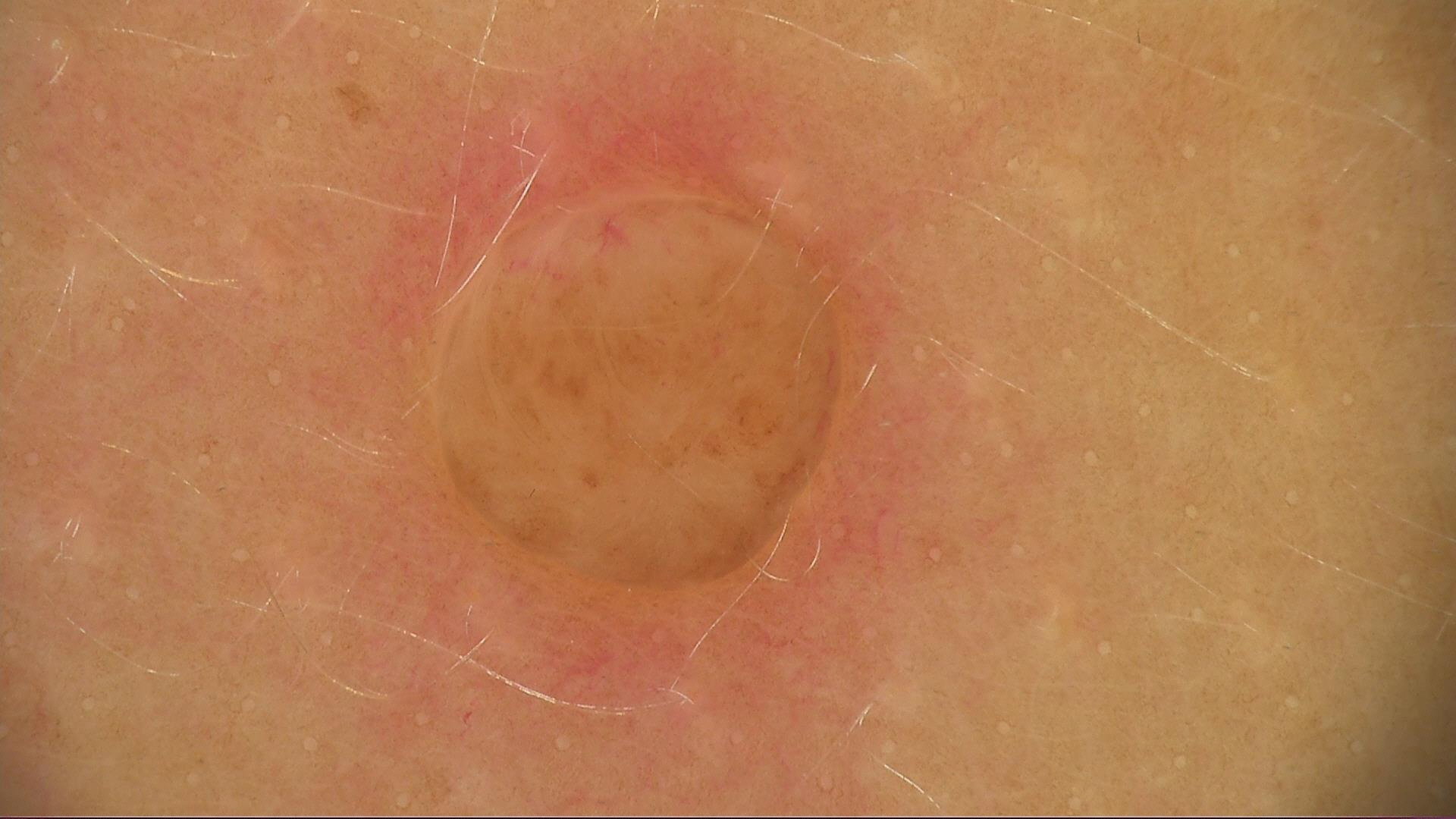image: dermoscopy
diagnosis:
  name: dermal nevus
  code: db
  malignancy: benign
  super_class: melanocytic
  confirmation: expert consensus